A dermoscopic photograph of a skin lesion.
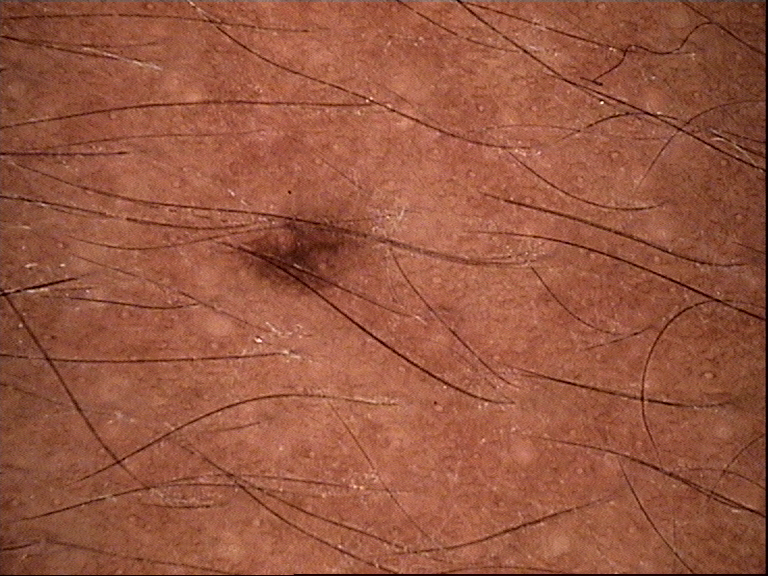Conclusion:
Classified as a junctional nevus.